The patient is a female aged 60–69, this image was taken at an angle, the affected area is the leg.
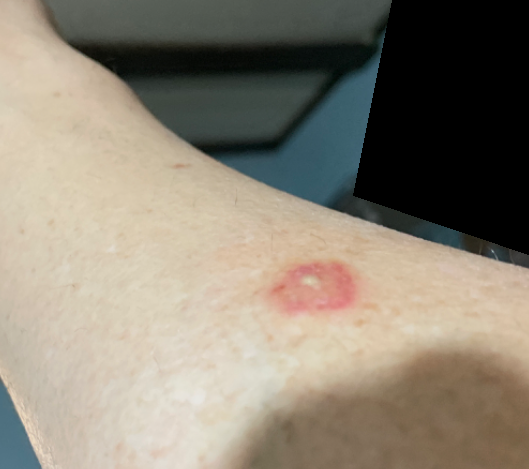  symptoms: enlargement
  patient_category: a rash
  texture:
    - raised or bumpy
    - fluid-filled
  differential:
    leading:
      - Insect Bite